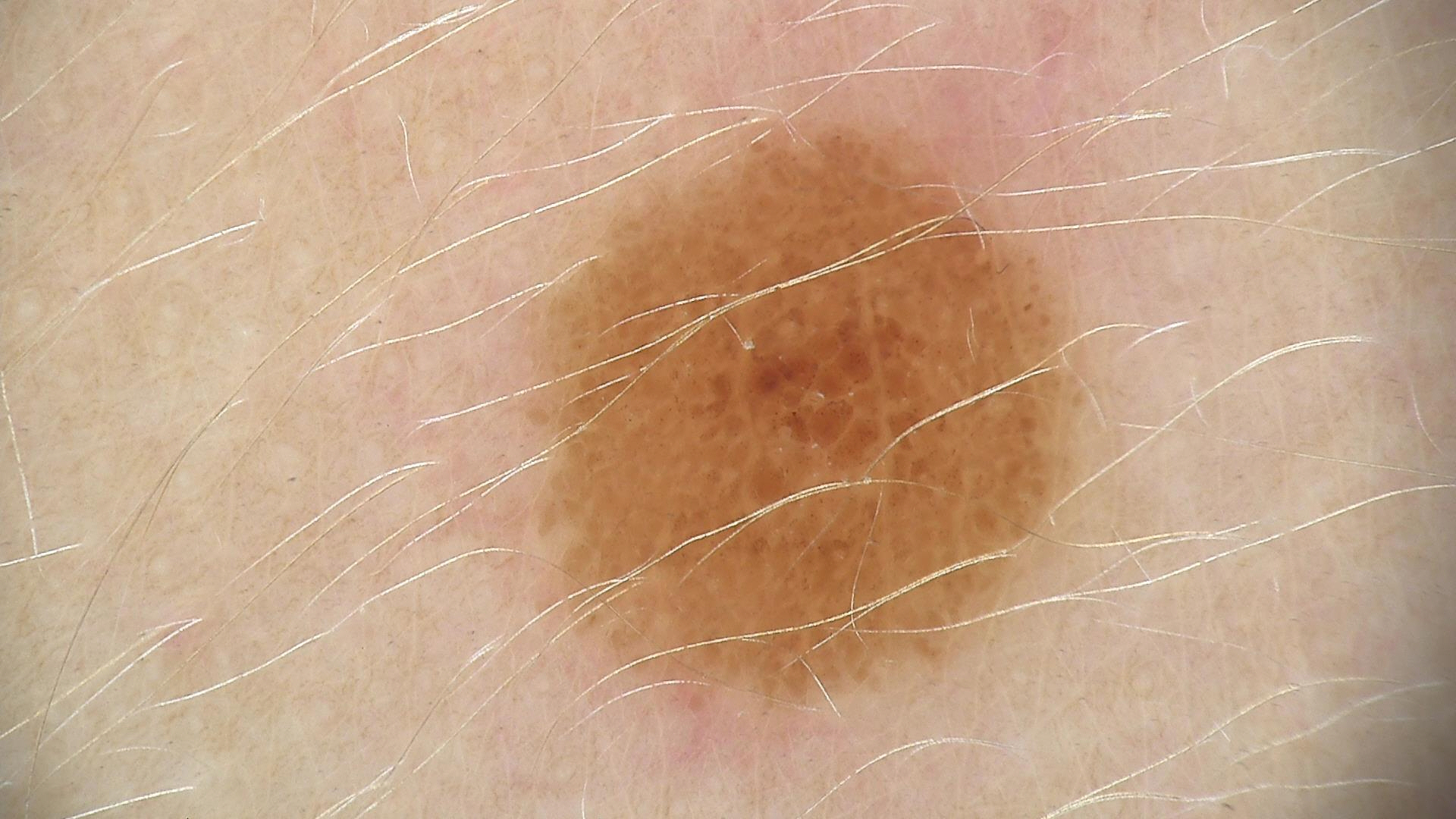A dermoscopic photograph of a skin lesion. Diagnosed as a benign lesion — a dysplastic compound nevus.